A smartphone photograph of a skin lesion; the chart notes prior malignancy (patient or family).
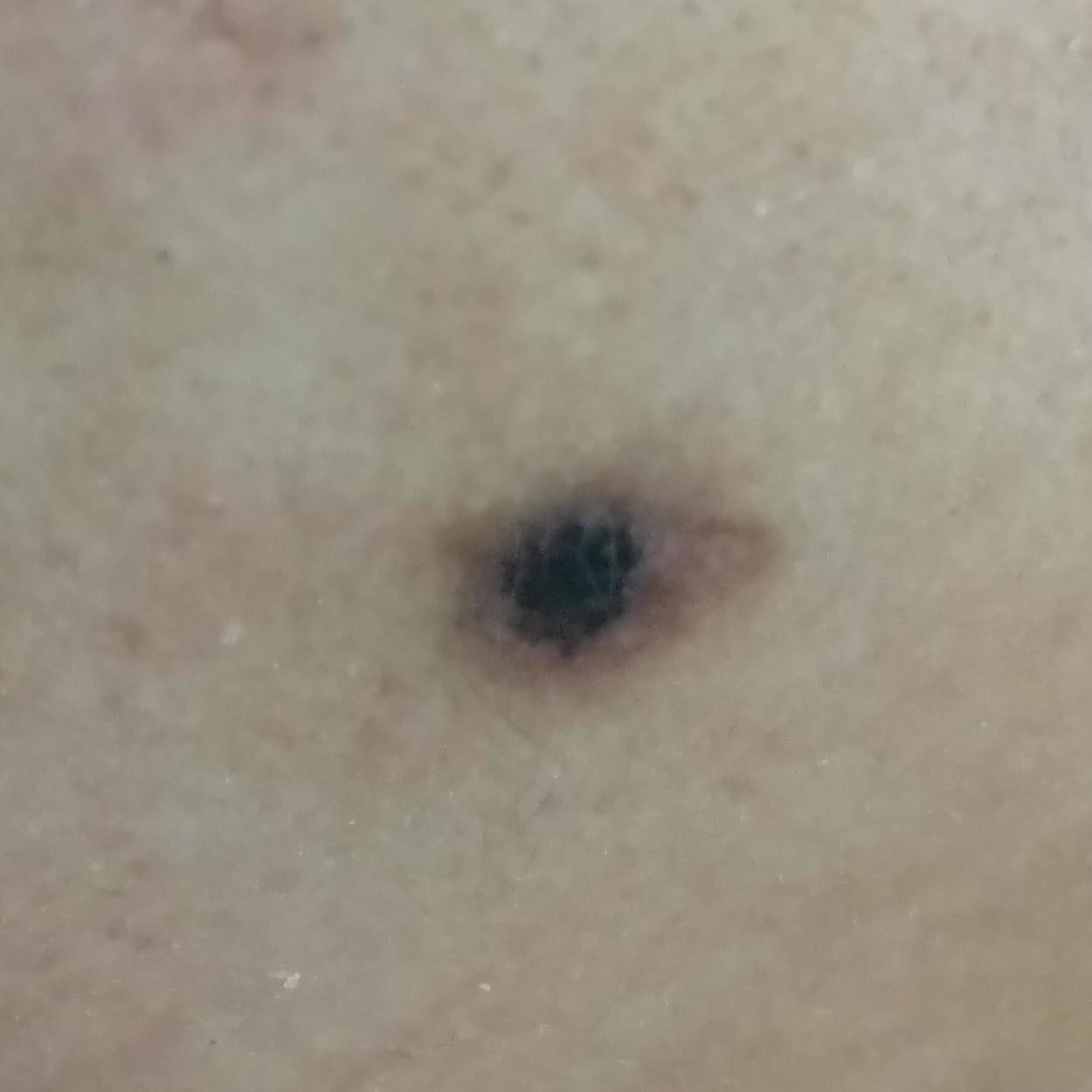Case:
* region · the face
* size · approx. 10 × 9 mm
* pathology · nevus (biopsy-proven)